This is a close-up image. The arm is involved. The patient is 30–39, female:
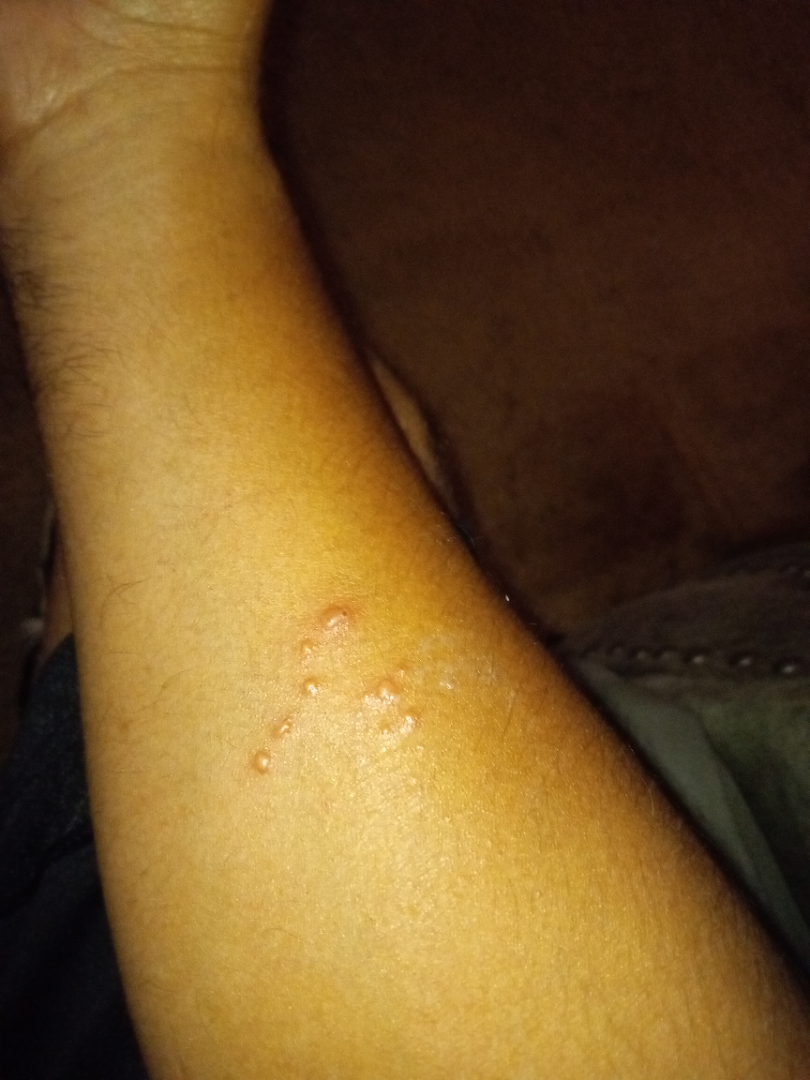The skin findings could not be characterized from the image.
Reported lesion symptoms include itching.
The patient indicates the lesion is flat.